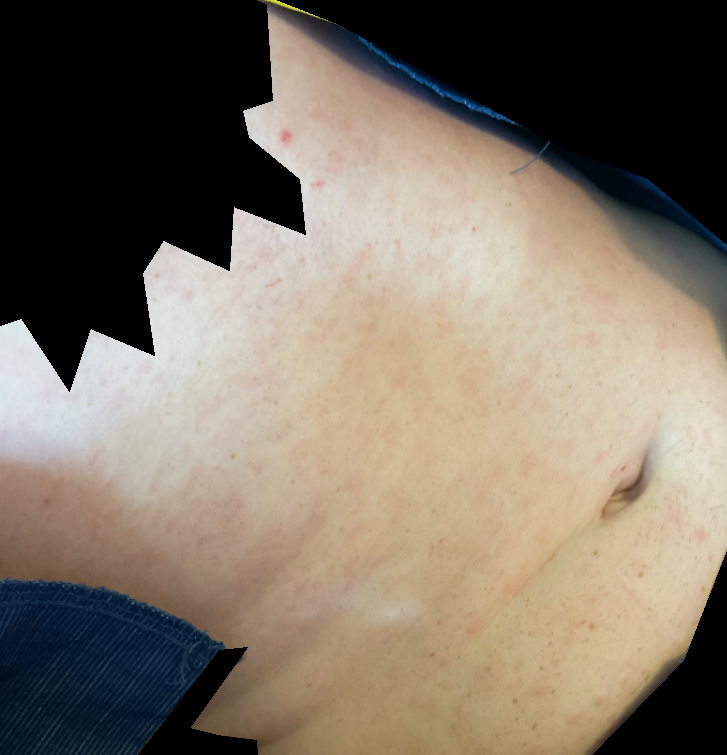image framing = at an angle, diagnostic considerations = Drug Rash (considered); Viral Exanthem (considered); Folliculitis (unlikely).